Recorded as Fitzpatrick skin type II; a dermatoscopic image of a skin lesion: 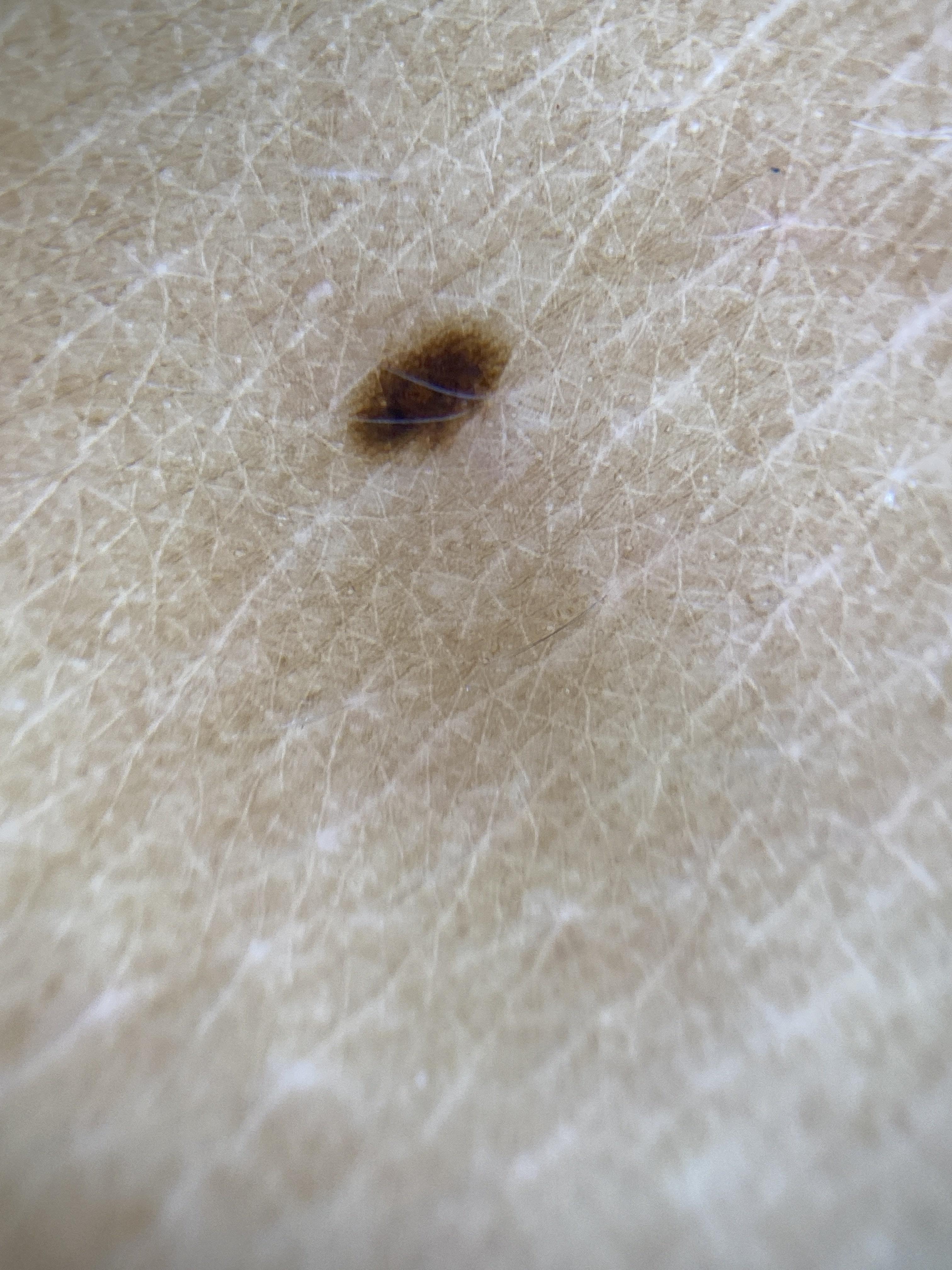The lesion is located on the trunk. The clinical impression was a benign, melanocytic lesion — a nevus.